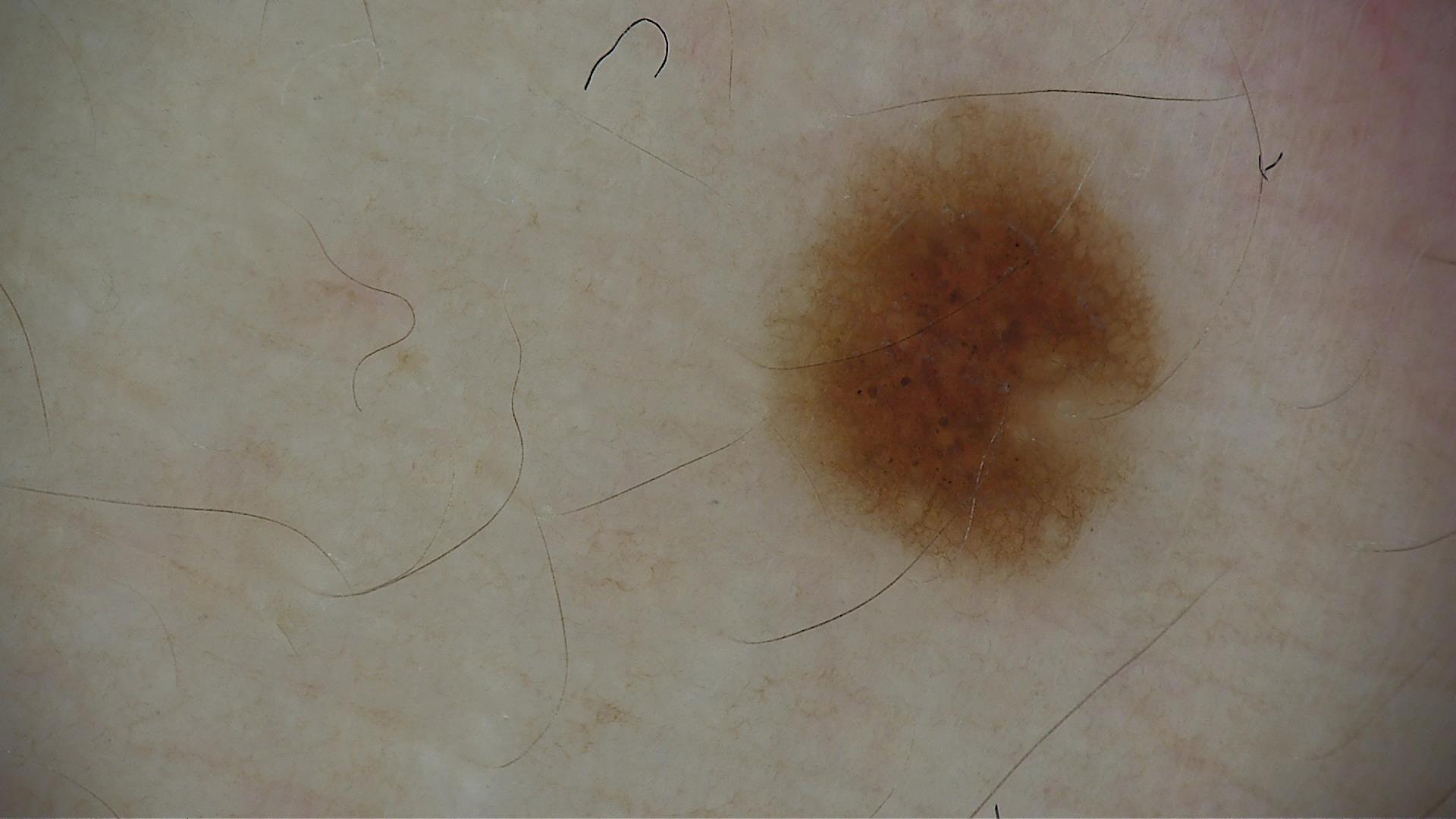Diagnosed as a benign lesion — a dysplastic junctional nevus.